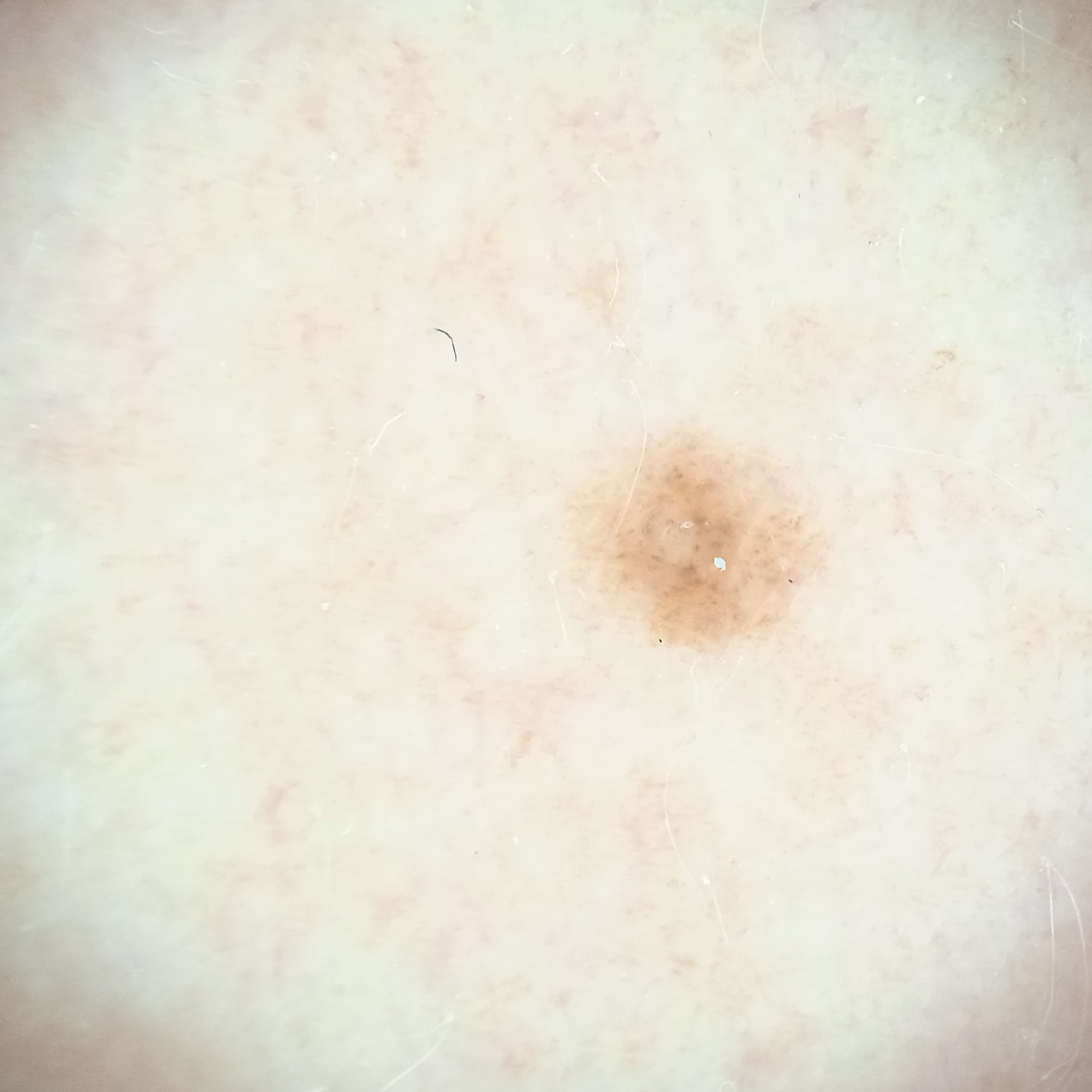<skin_lesion>
  <image>dermoscopy</image>
  <referral>research study (no referral diagnosis)</referral>
  <patient>
    <age>48</age>
    <sex>female</sex>
  </patient>
  <diagnosis>
    <name>melanocytic nevus</name>
    <malignancy>benign</malignancy>
  </diagnosis>
</skin_lesion>